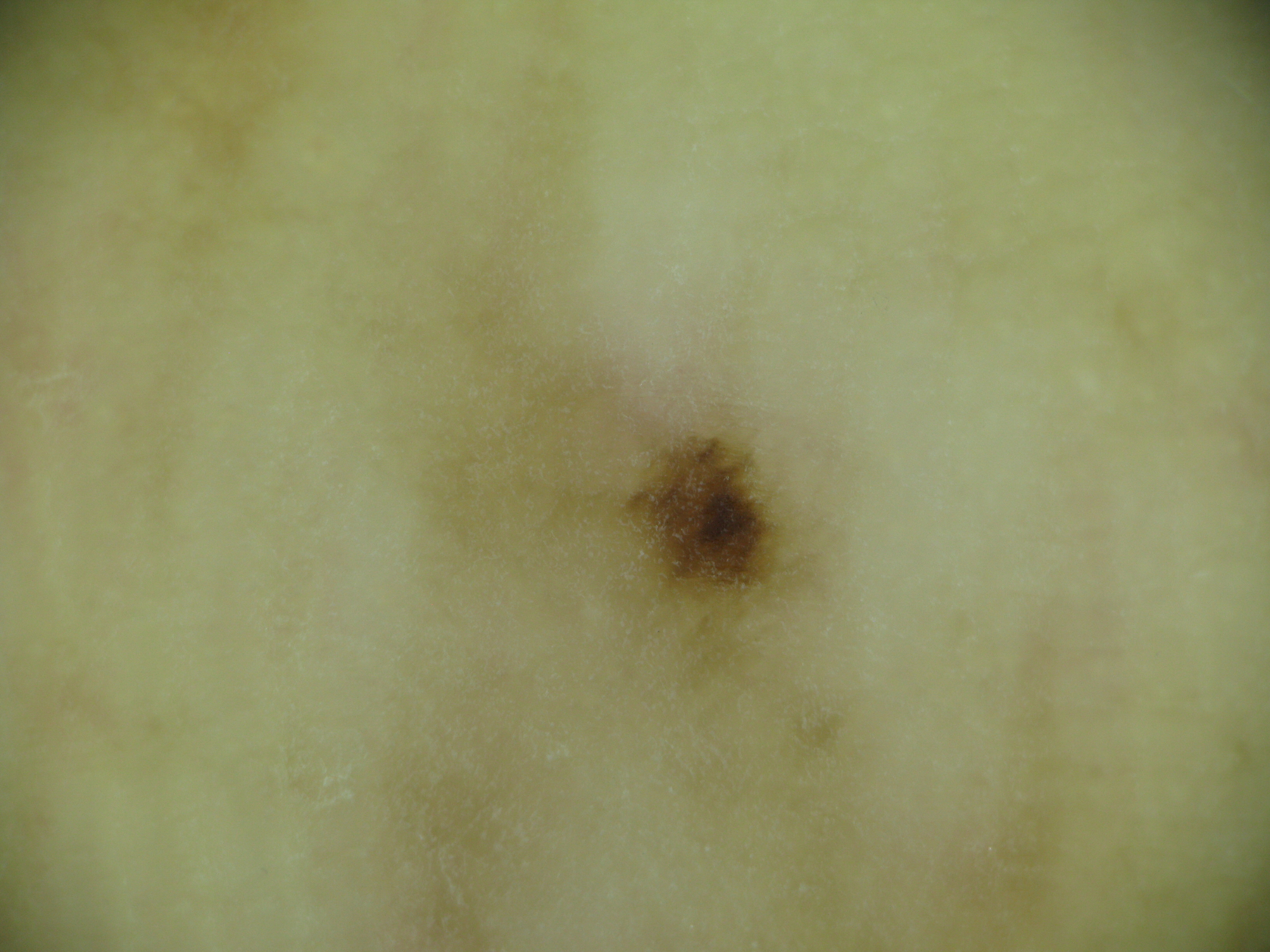A skin lesion imaged with a dermatoscope. The diagnostic label was an acral dysplastic junctional nevus.